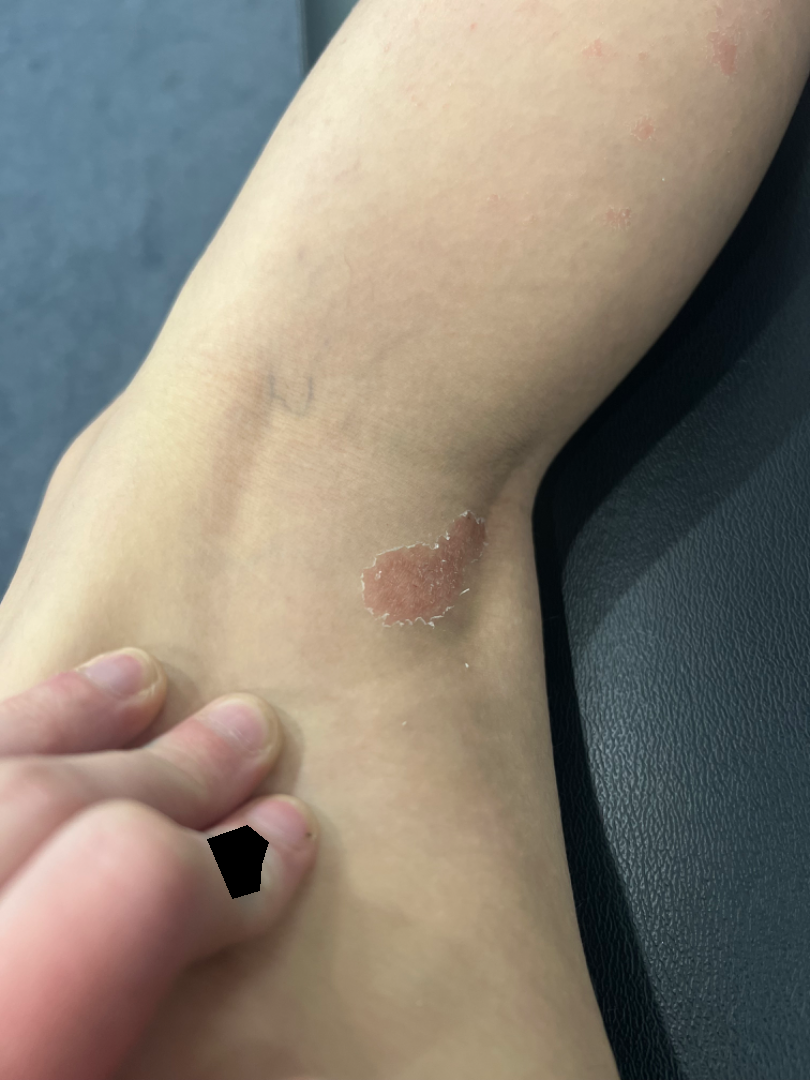- constitutional symptoms: none reported
- shot type: at a distance
- texture: raised or bumpy and rough or flaky
- self-categorized as: a rash
- anatomic site: leg
- duration: one to four weeks
- impression: the favored diagnosis is Eczema